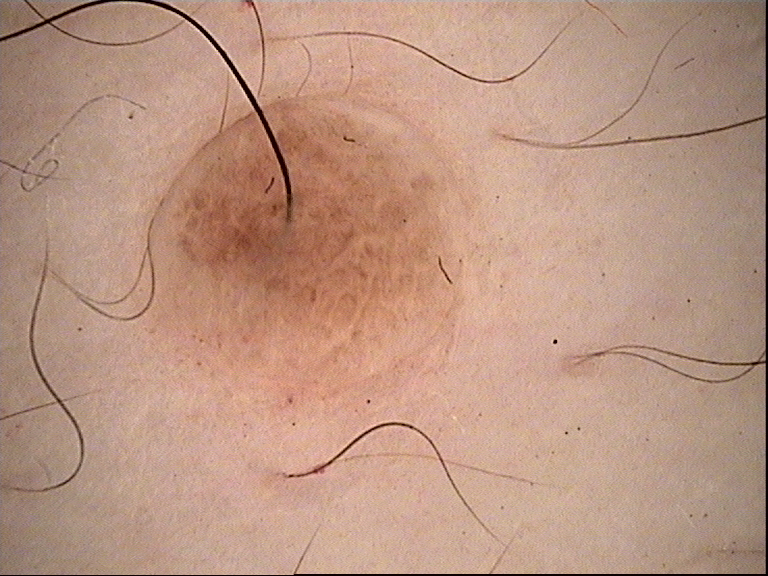Findings:
* imaging · dermoscopy
* diagnosis · dermal nevus (expert consensus)